A skin lesion imaged with a dermatoscope:
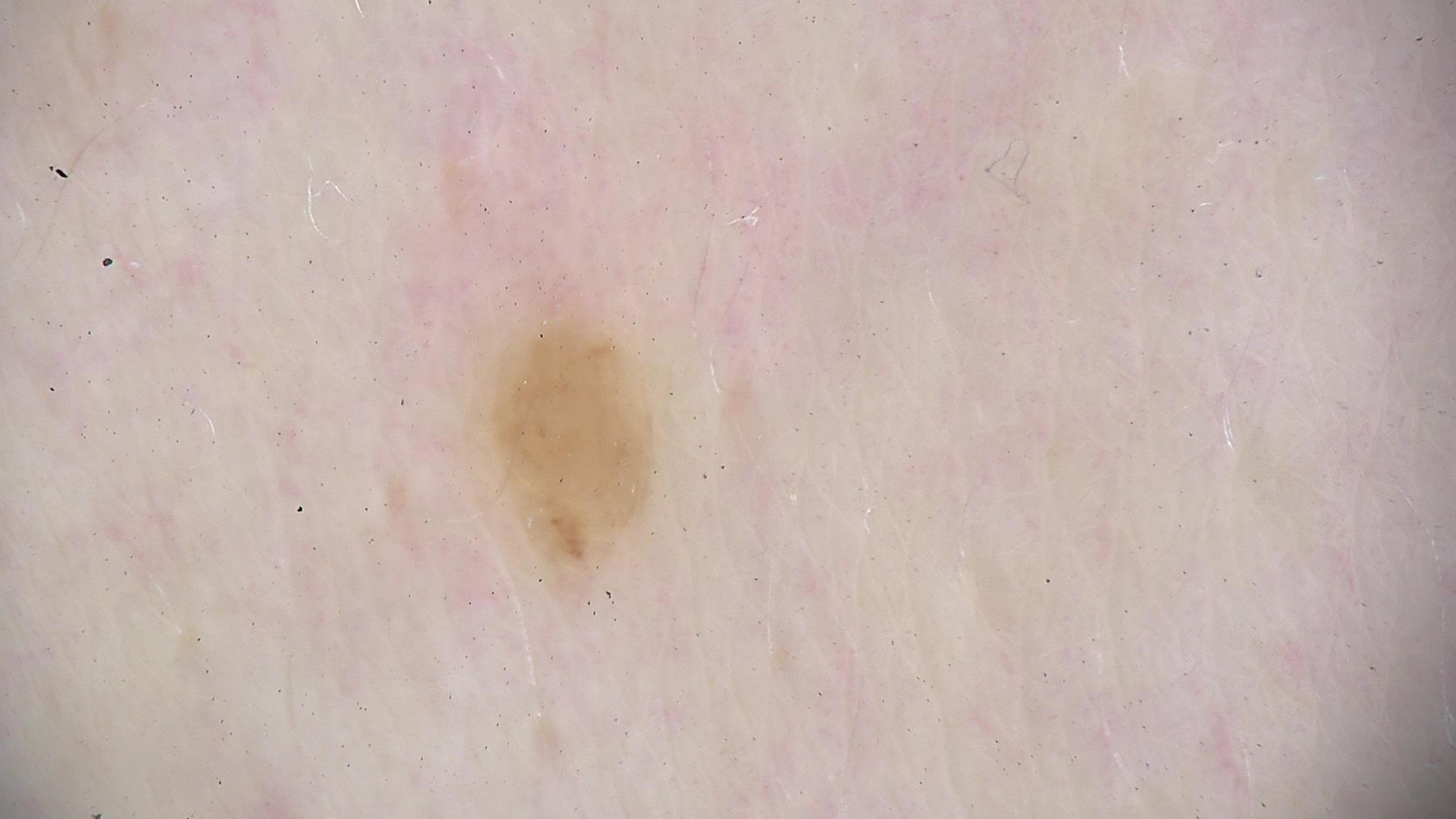Q: What is this lesion?
A: dysplastic junctional nevus (expert consensus)